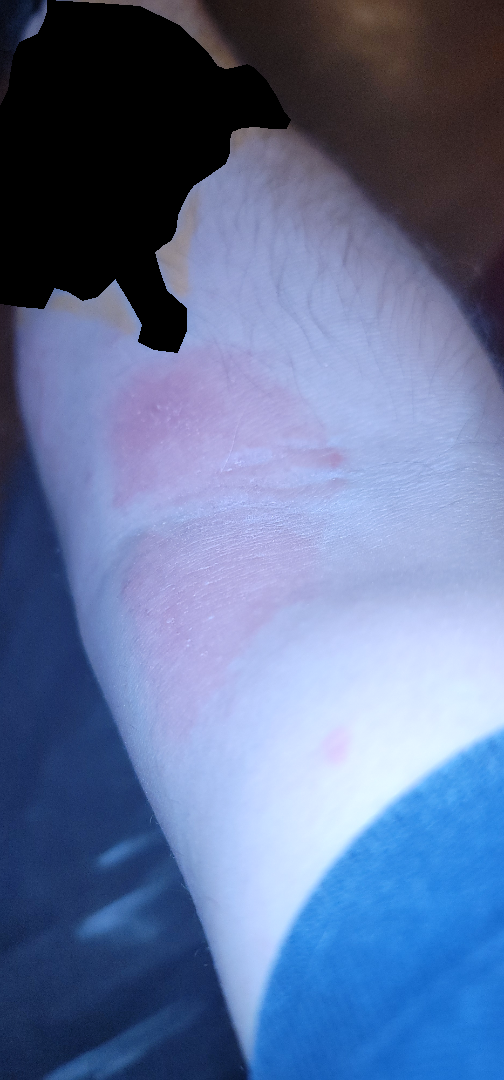The photo was captured at an angle. The front of the torso and arm are involved. On remote dermatologist review: the leading consideration is Eczema; the differential also includes Tinea; also raised was Psoriasis.